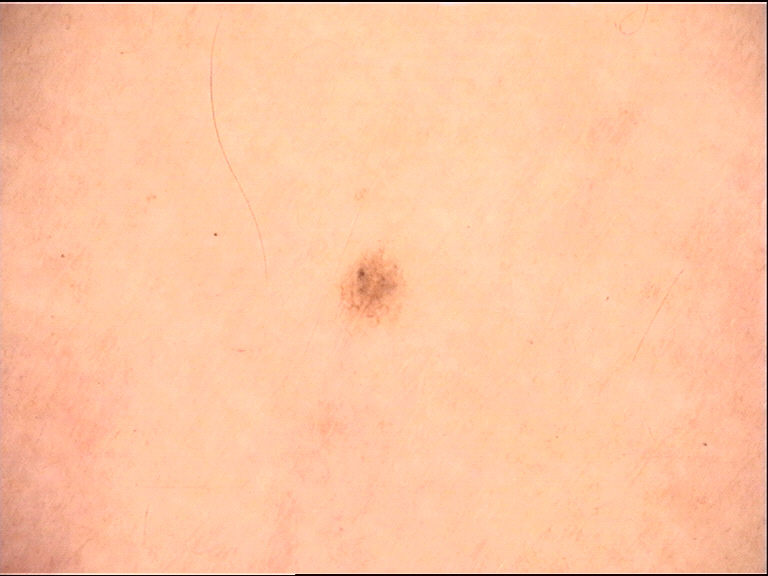Conclusion: The diagnostic label was a benign lesion — a dysplastic junctional nevus.